A dermatoscopic image of a skin lesion: 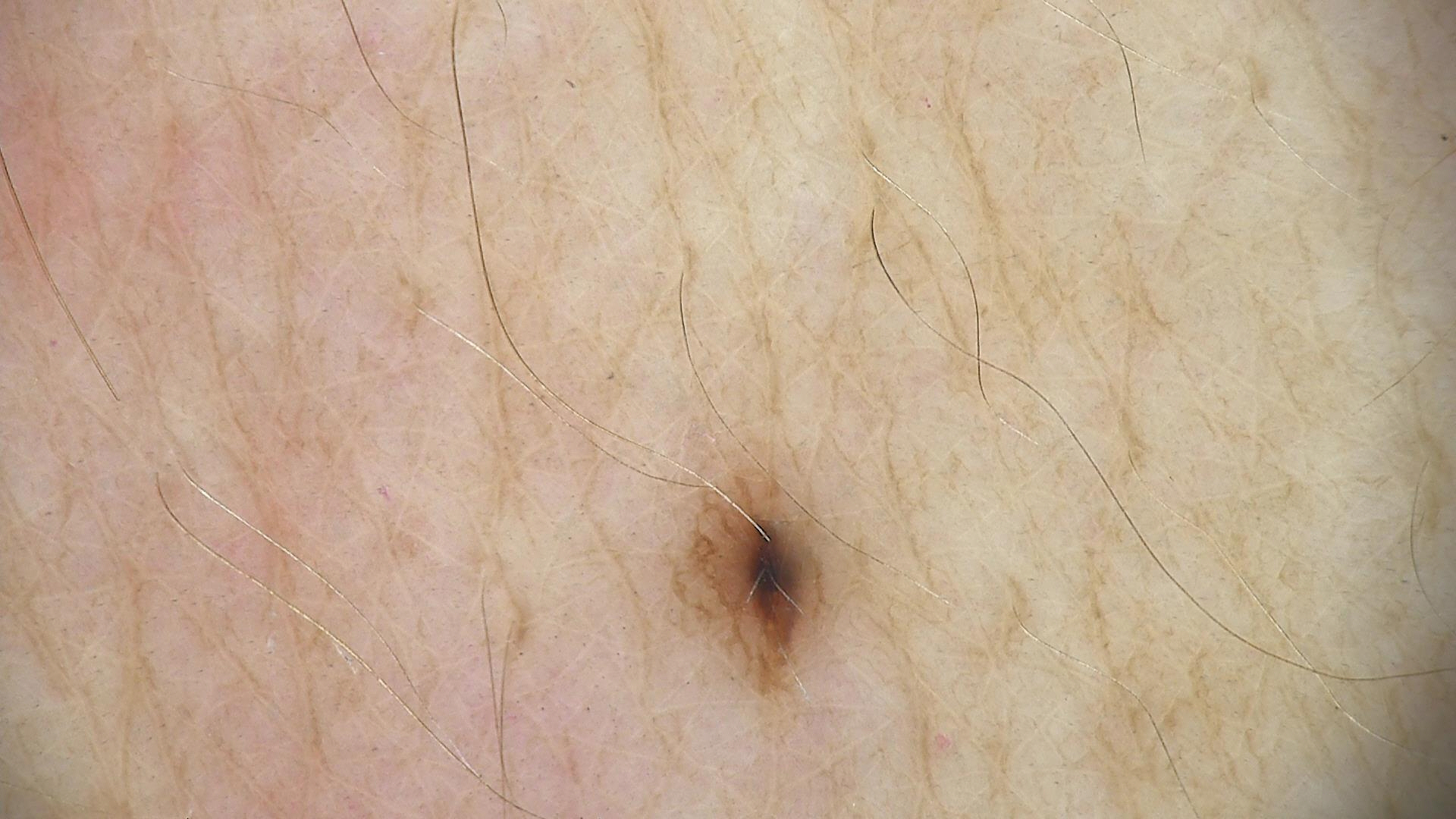Diagnosed as a benign lesion — a dysplastic junctional nevus.